This image was taken at an angle:
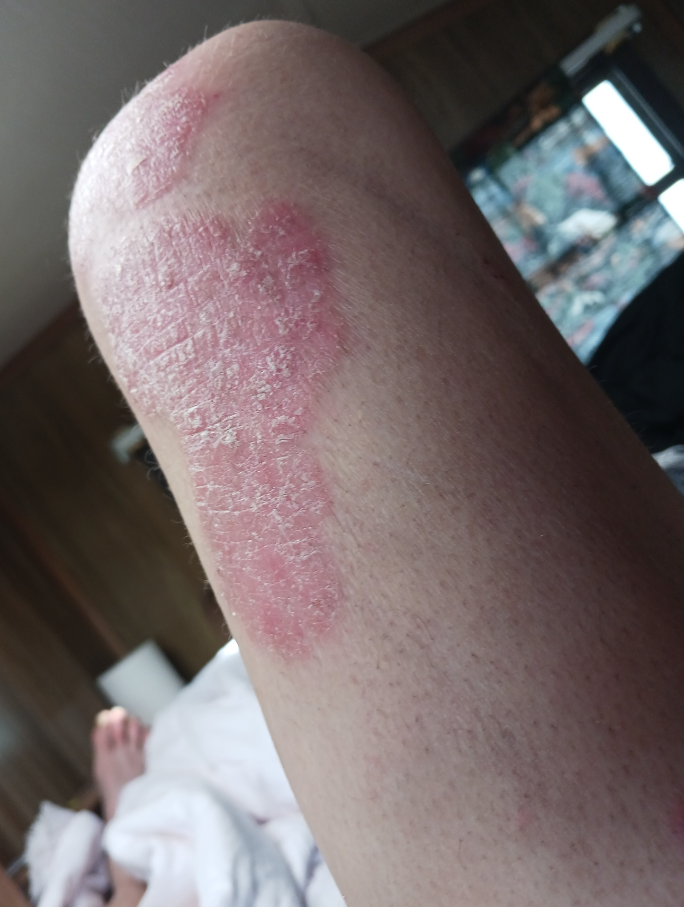One reviewing dermatologist: consistent with Psoriasis.